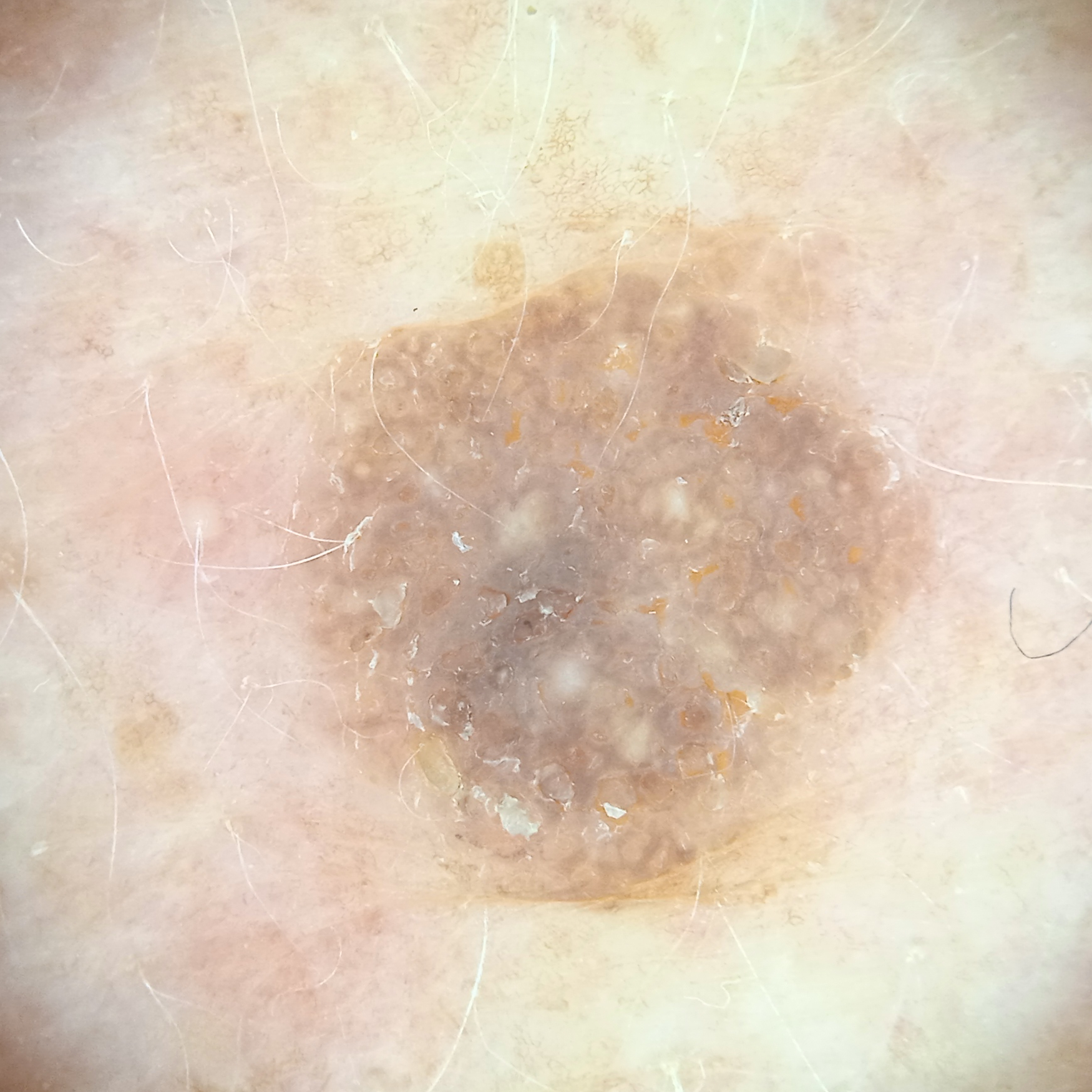Case:
- nevus count · numerous melanocytic nevi
- patient · female, 78 years old
- referral context · research study (no referral diagnosis)
- imaging · dermatoscopic image
- sun reaction · skin tans without first burning
- site · the back
- diagnostic label · seborrheic keratosis (dermatologist consensus)